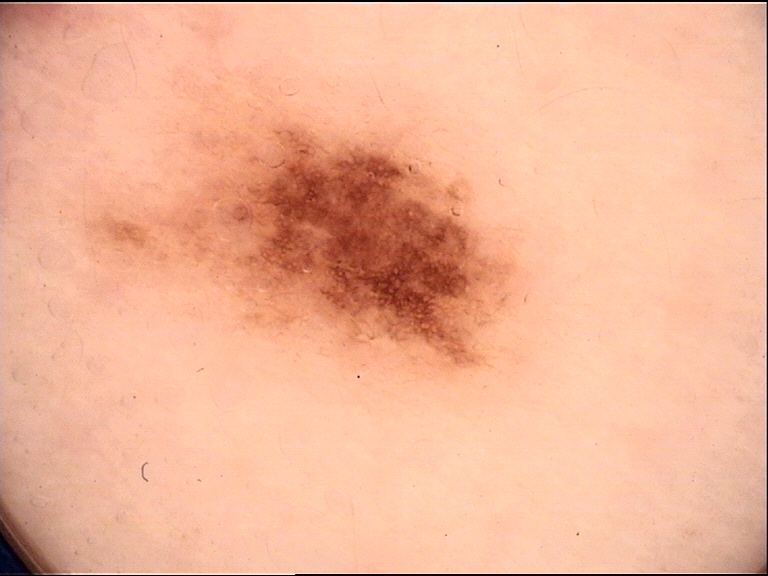Conclusion:
Labeled as a dysplastic junctional nevus.